A skin lesion imaged with a dermatoscope.
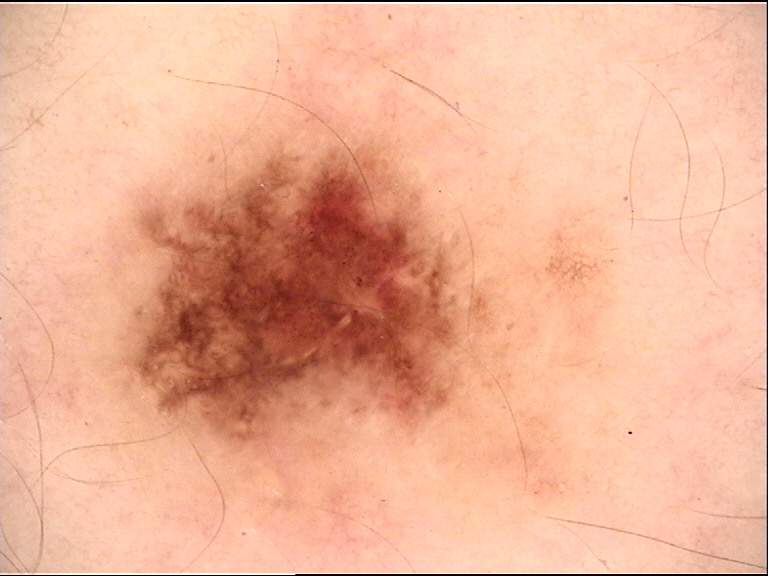Conclusion: Labeled as a dysplastic junctional nevus.